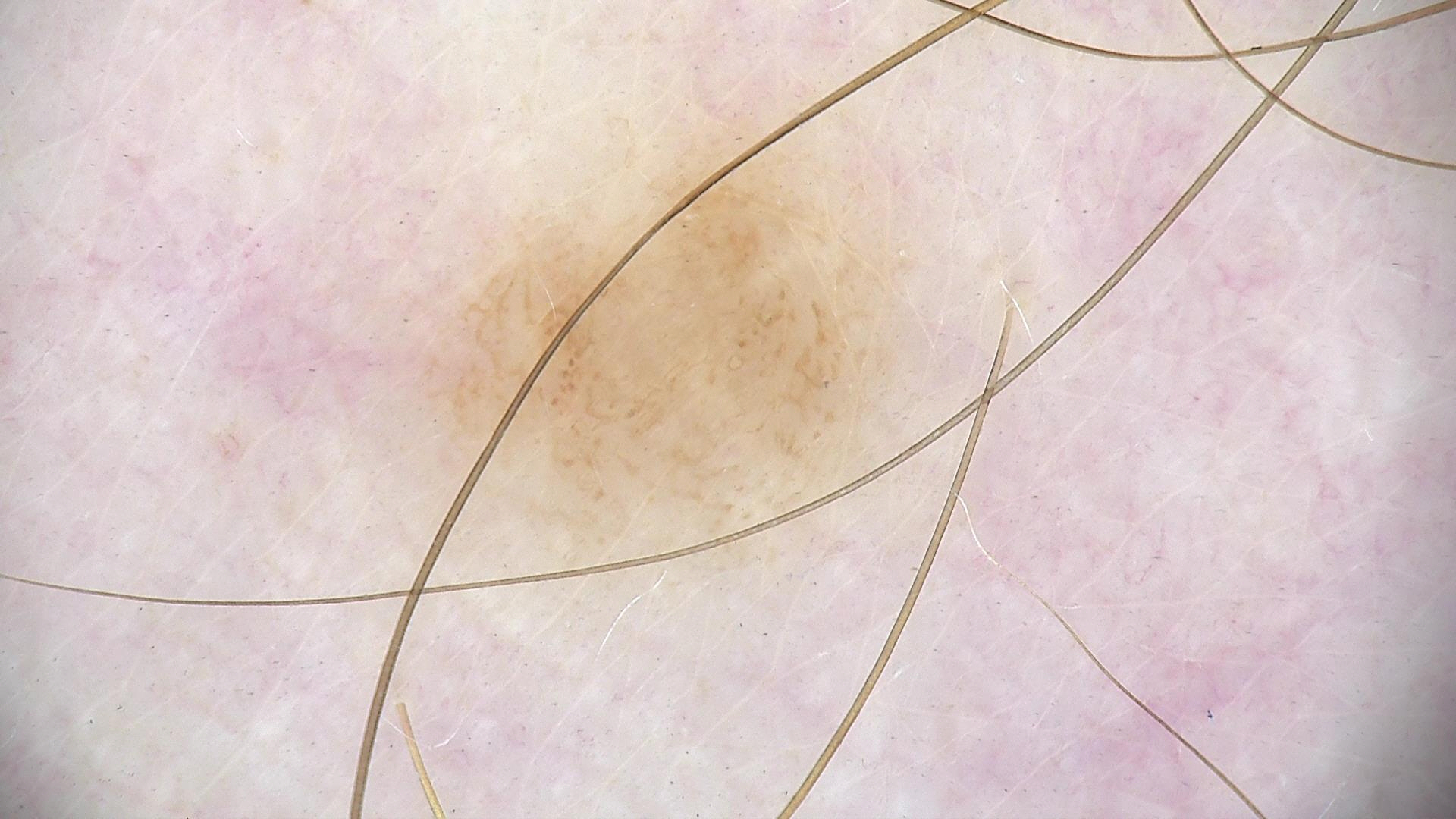Diagnosed as a dysplastic junctional nevus.